Located on the back of the torso. This is a close-up image:
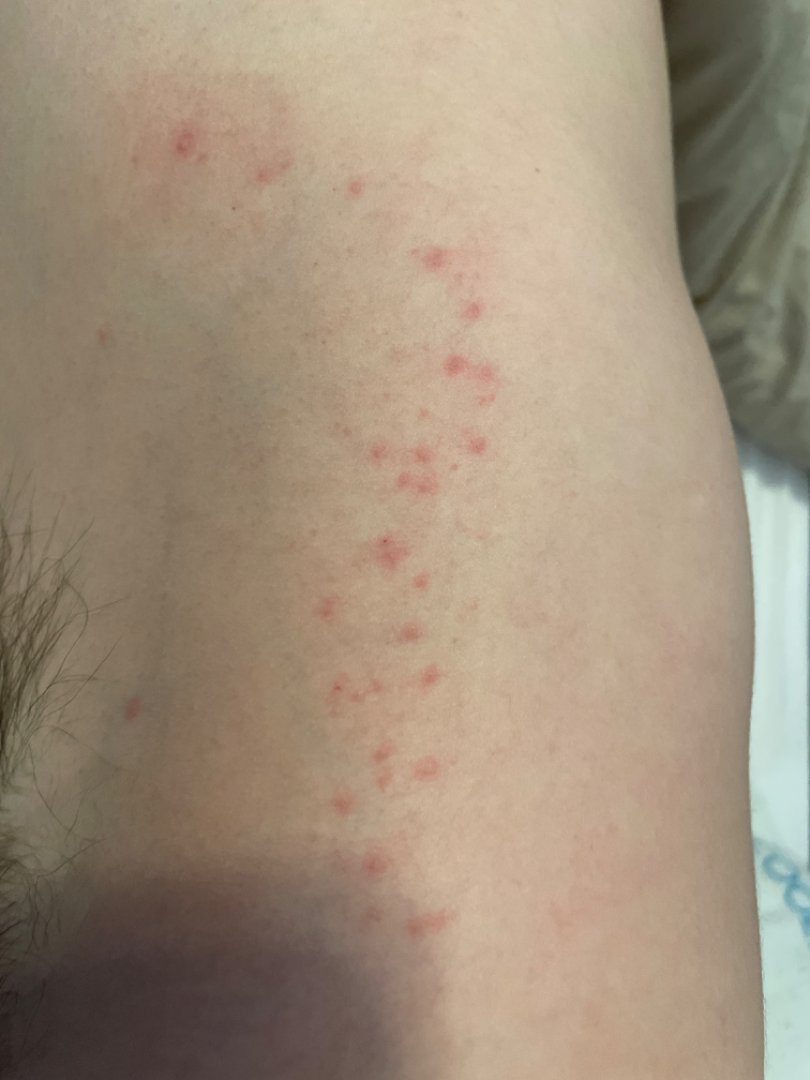Q: How does the lesion feel?
A: raised or bumpy
Q: What symptoms does the patient report?
A: itching and bothersome appearance
Q: Any systemic symptoms?
A: none reported
Q: Patient's own categorization?
A: a rash
Q: What is the dermatologist's impression?
A: Insect Bite (0.41); Allergic Contact Dermatitis (0.41); Eczema (0.18)